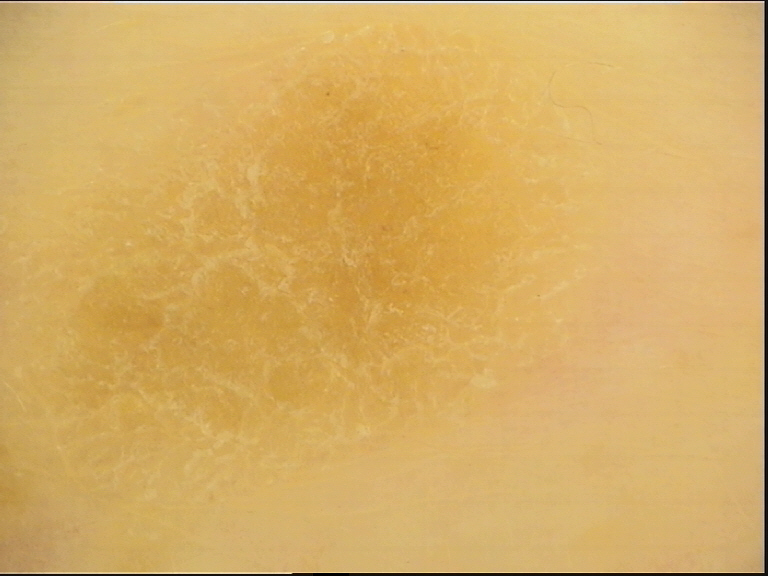diagnosis:
  name: seborrheic keratosis
  code: sk
  malignancy: benign
  super_class: non-melanocytic
  confirmation: expert consensus